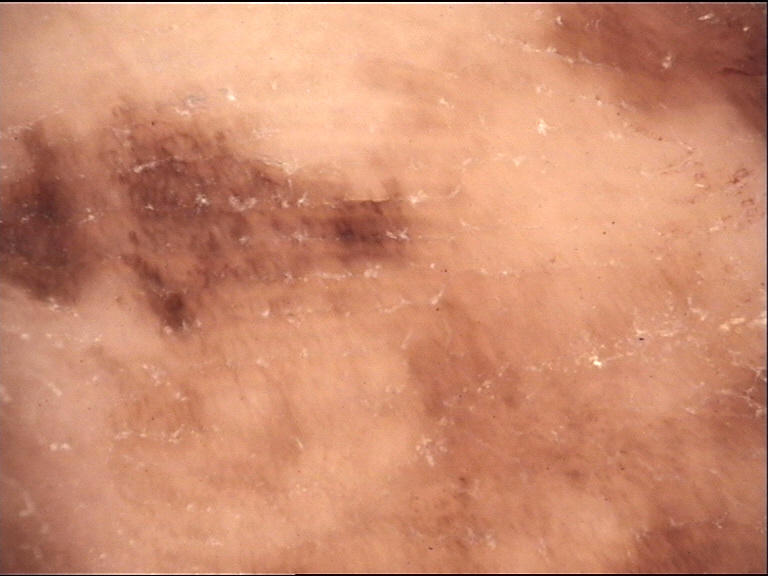A dermoscopic close-up of a skin lesion.
Histopathologically confirmed as an acral lentiginous melanoma.